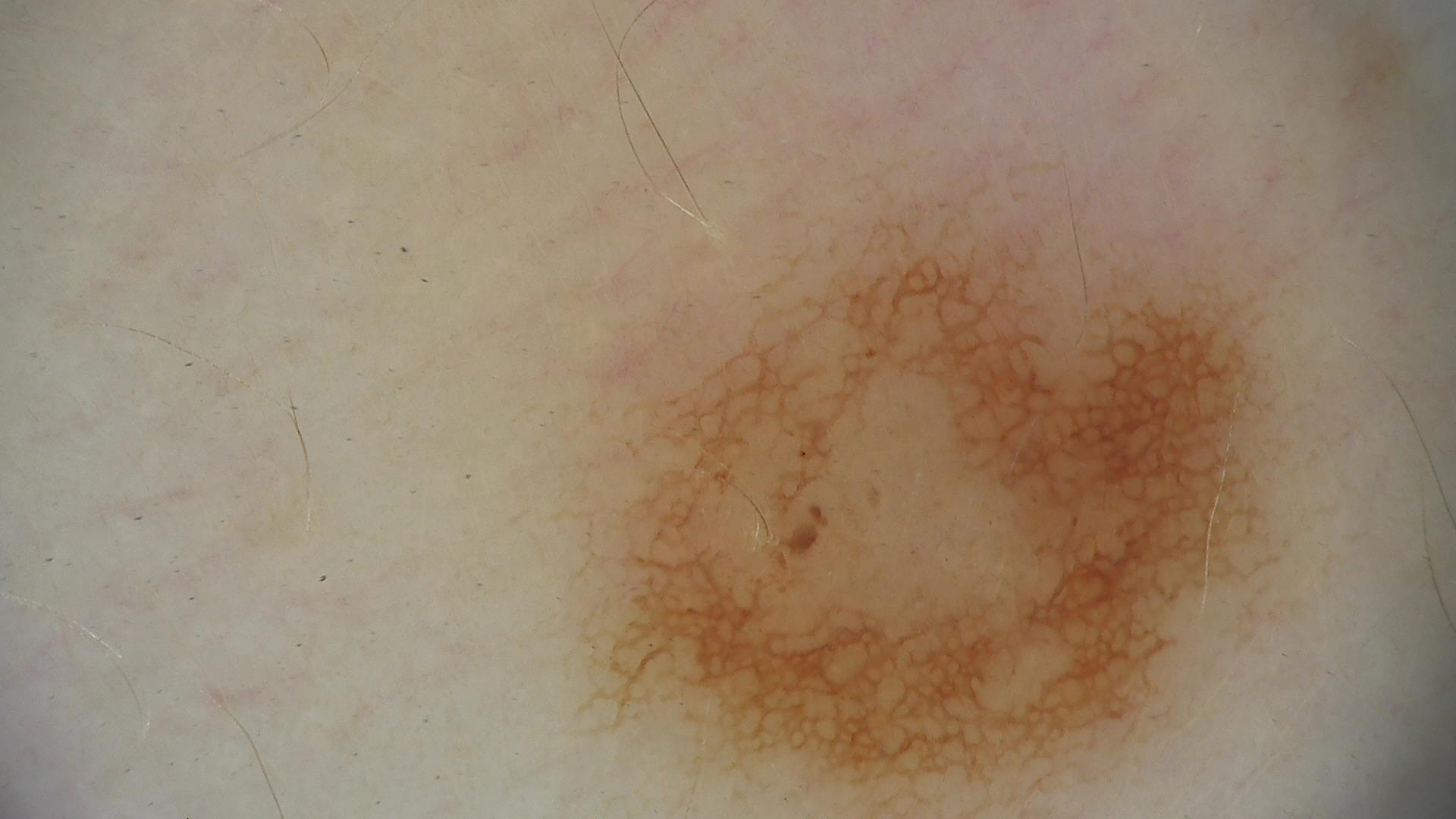Impression:
Consistent with a dysplastic junctional nevus.